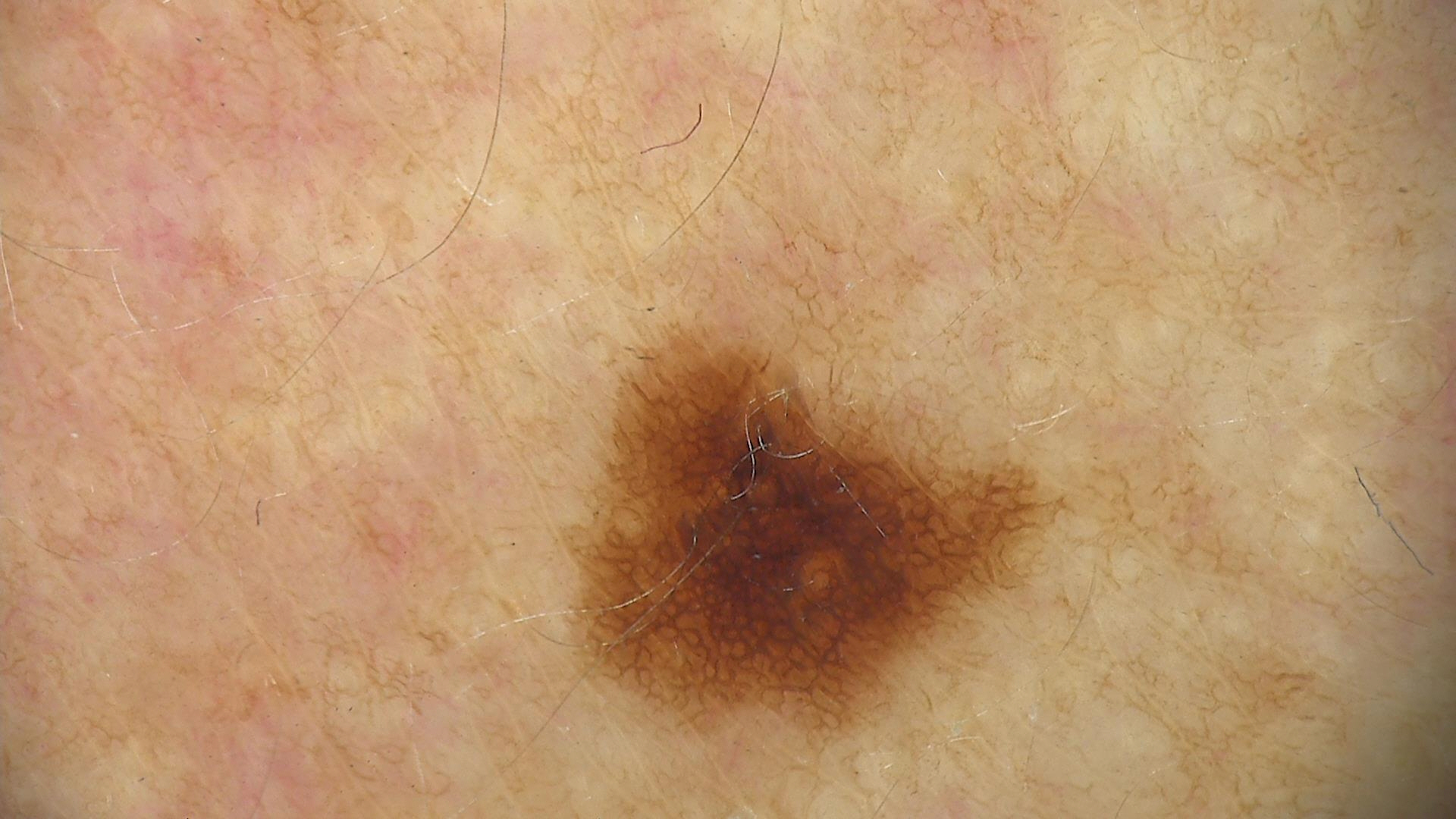Dermoscopy of a skin lesion. Consistent with a dysplastic junctional nevus.